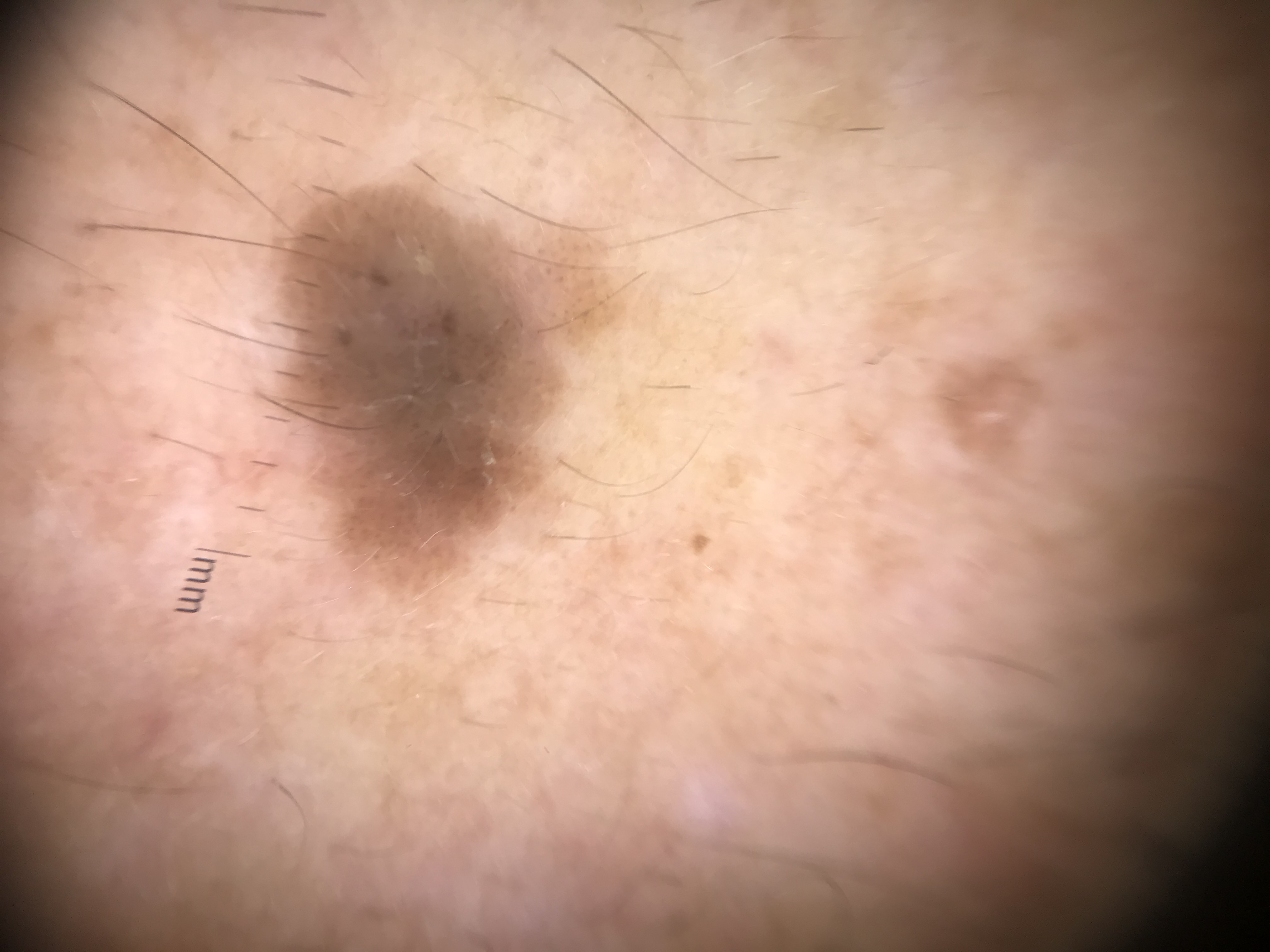The diagnosis was a seborrheic keratosis.